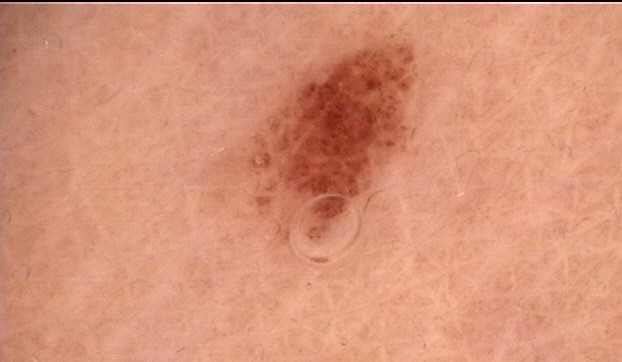Summary: A skin lesion imaged with a dermatoscope. The architecture is that of a banal lesion. Conclusion: Diagnosed as a junctional nevus.